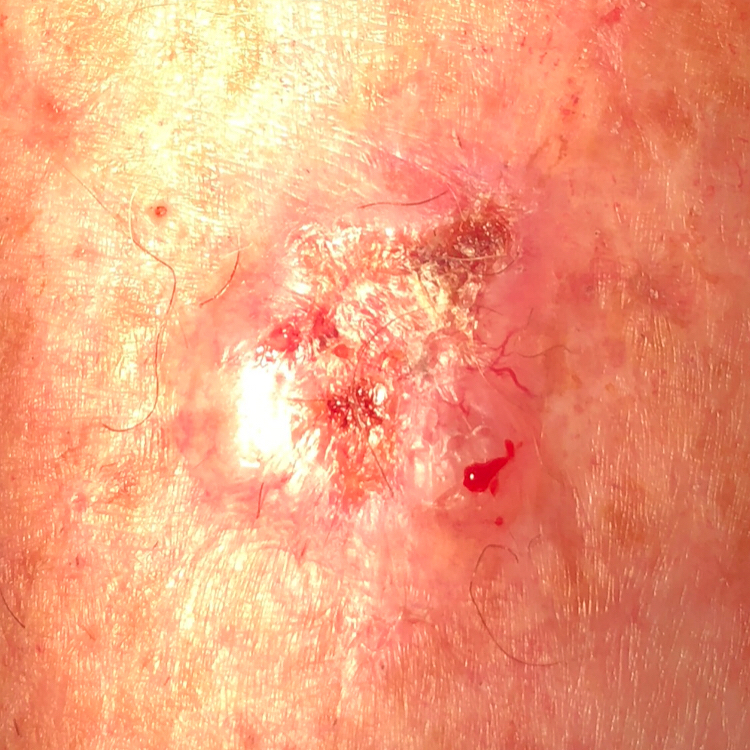Summary: The chart records prior malignancy (patient or family). A clinical photograph of a skin lesion. A male subject aged 69. The lesion is on a forearm. The lesion is roughly 18 by 18 mm. Conclusion: On biopsy, the diagnosis was a basal cell carcinoma.